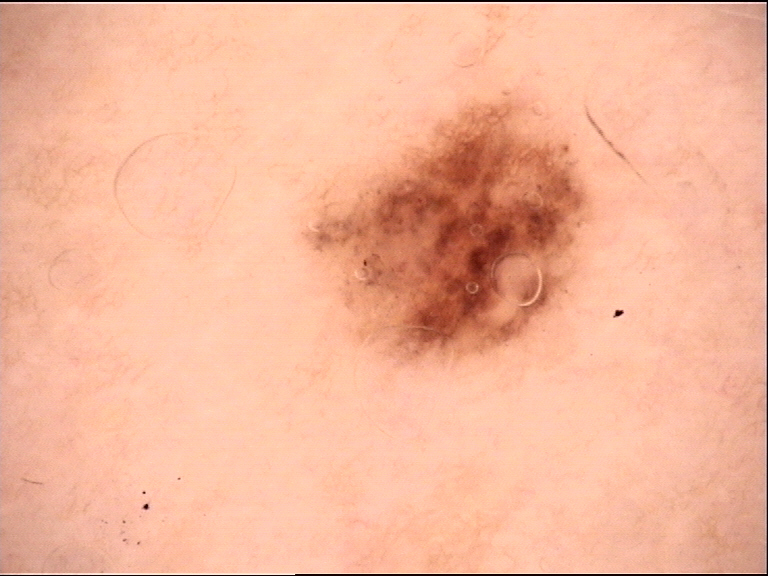Classified as a dysplastic junctional nevus.